A dermoscopic image of a skin lesion: 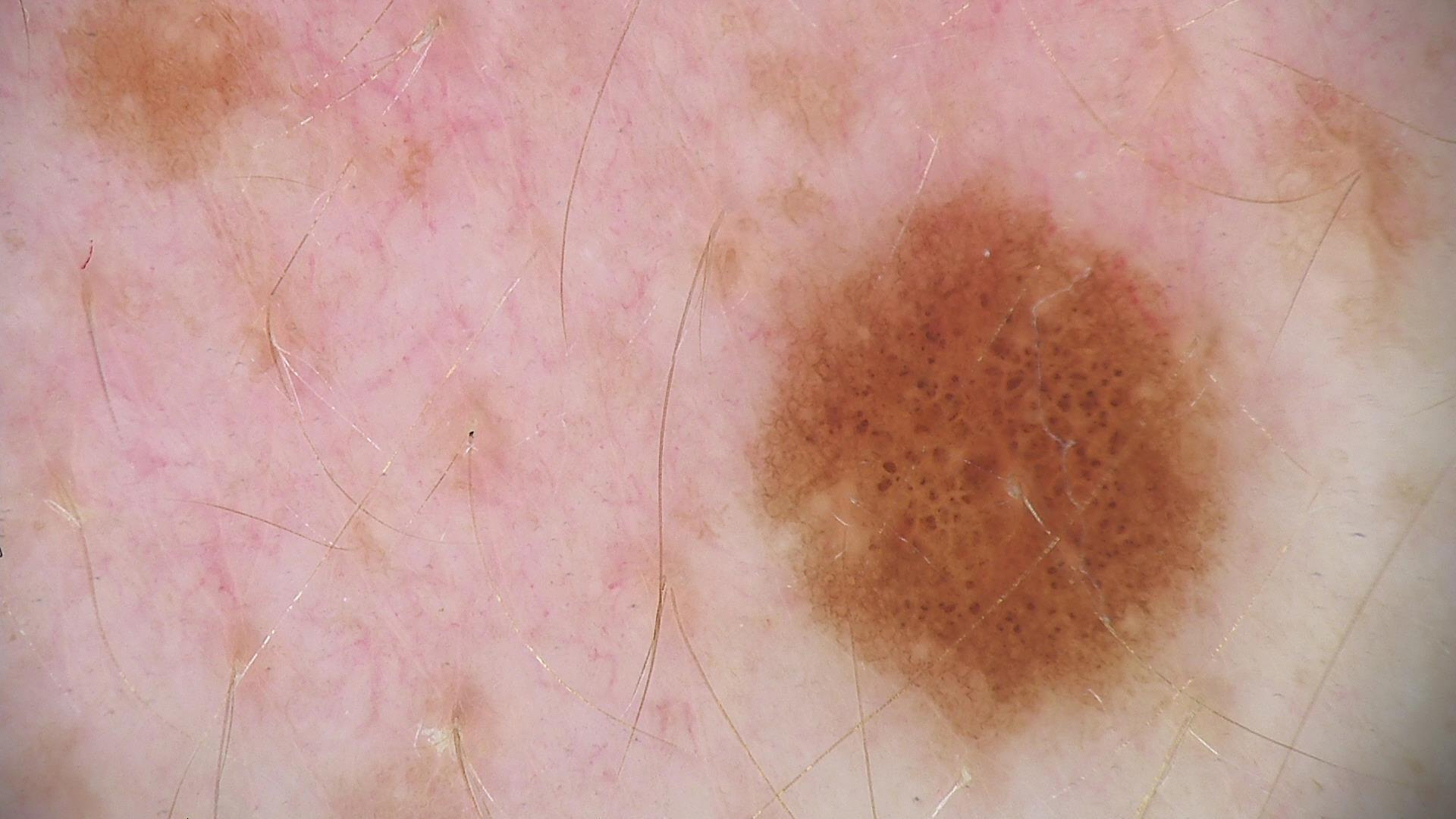class: dysplastic junctional nevus (expert consensus).